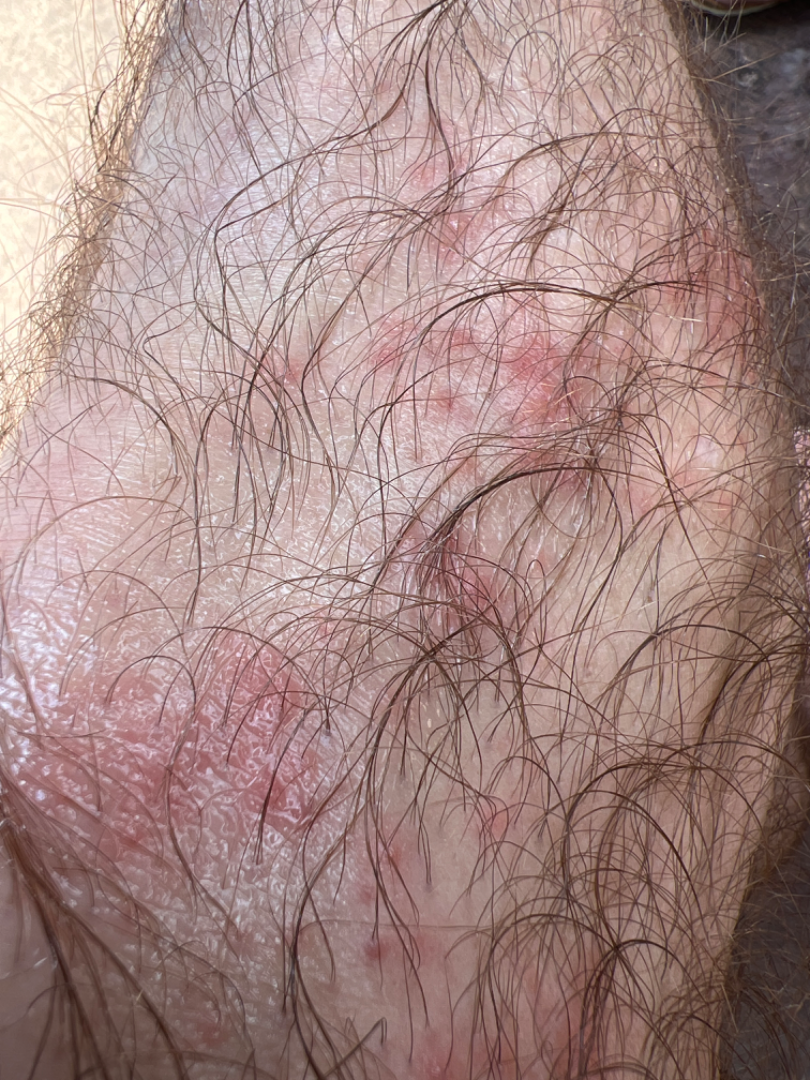Findings:
* assessment: not assessable